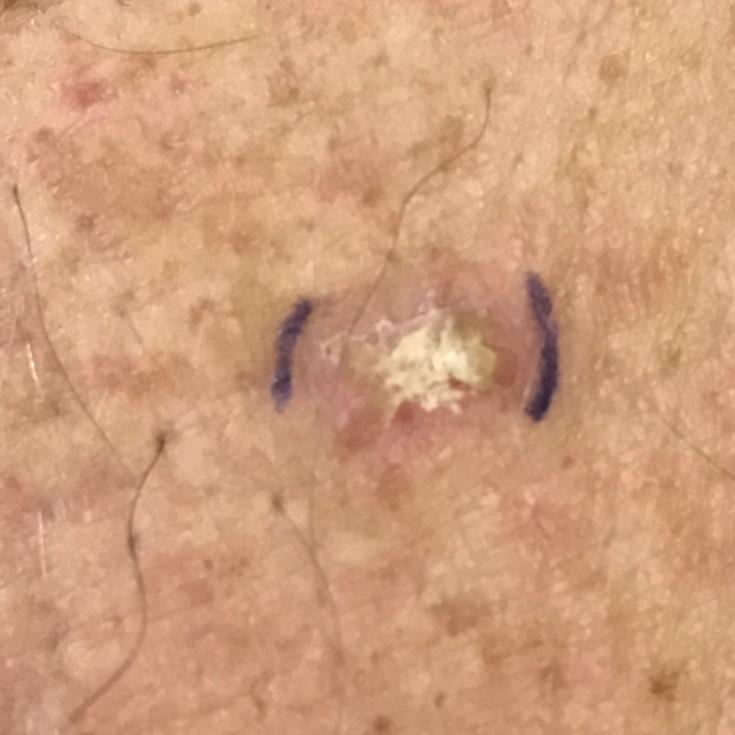patient = male, in their mid-40s
FST = II
exposures = pesticide exposure, alcohol use, prior skin cancer (patient or family)
location = an arm
diameter = 7 × 5 mm
reported symptoms = itching, elevation / no change in appearance, no bleeding
diagnosis = actinic keratosis (clinical consensus)